The affected area is the leg. The photo was captured at a distance. The contributor is 40–49, female — 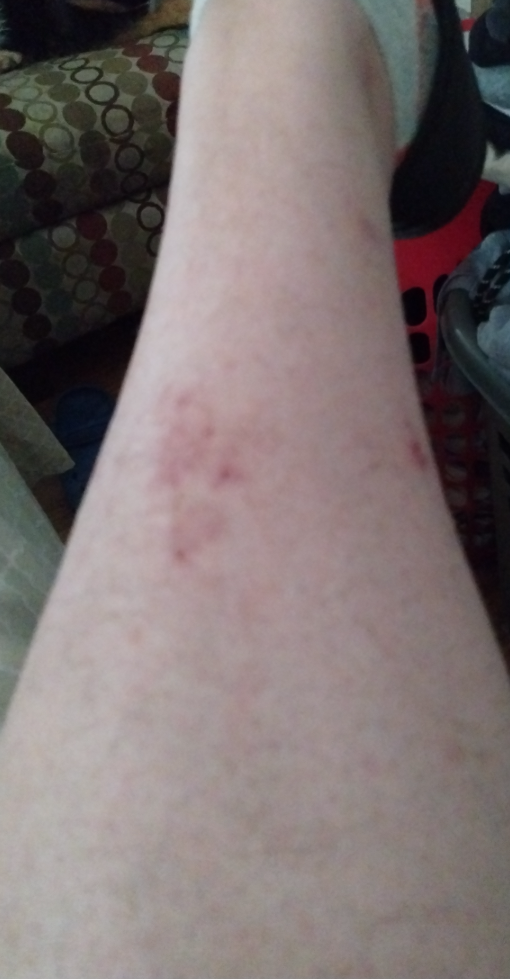assessment = indeterminate from the photograph